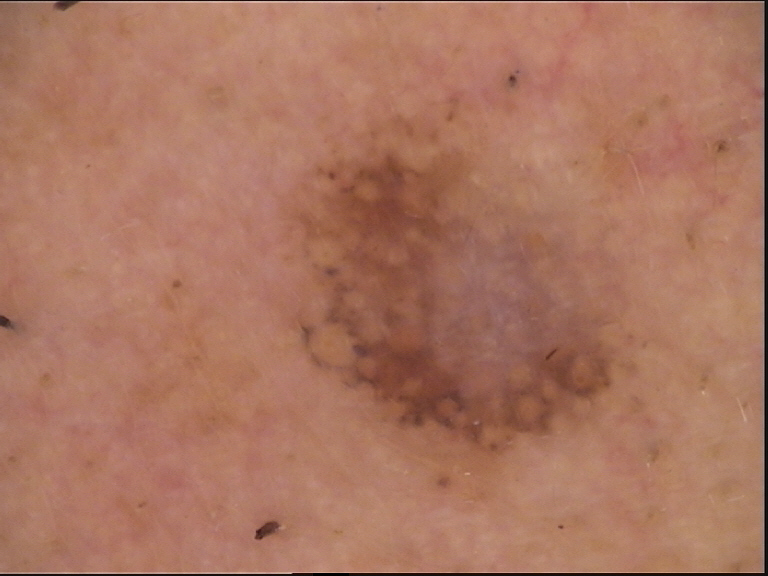A dermoscopic image of a skin lesion. Histopathology confirmed a lentigo maligna.